An image taken at a distance, the back of the torso is involved.
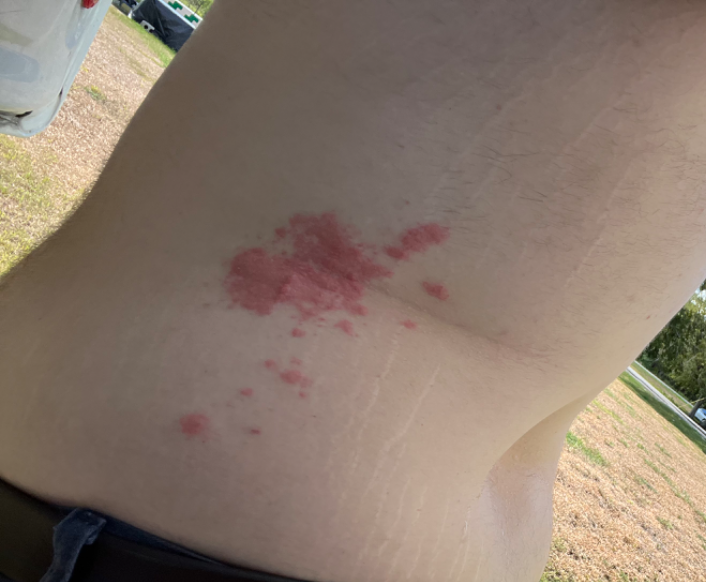| key | value |
|---|---|
| assessment | unable to determine |
| patient's own categorization | a rash |
| history | less than one week |